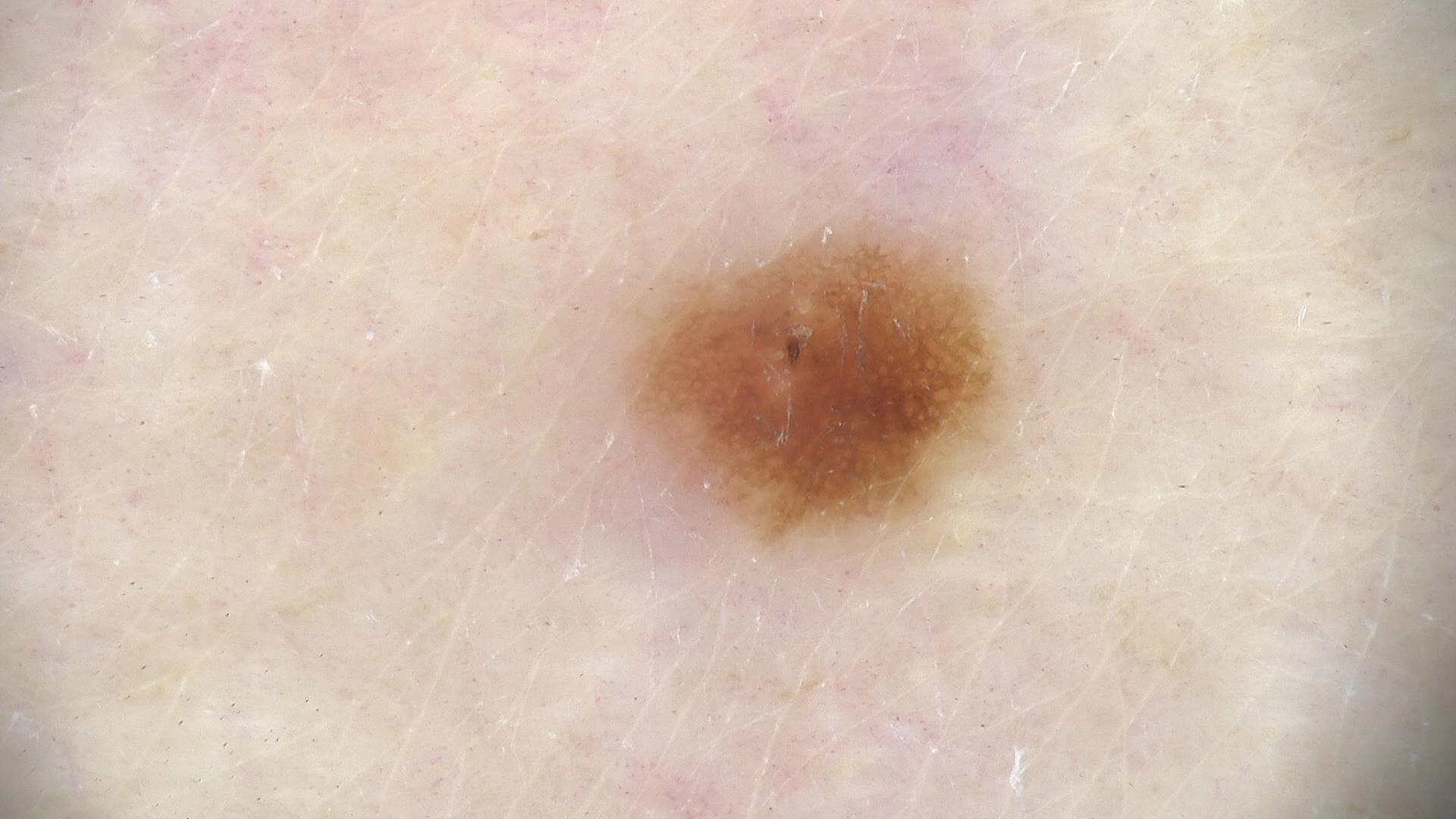– class · junctional nevus (expert consensus)